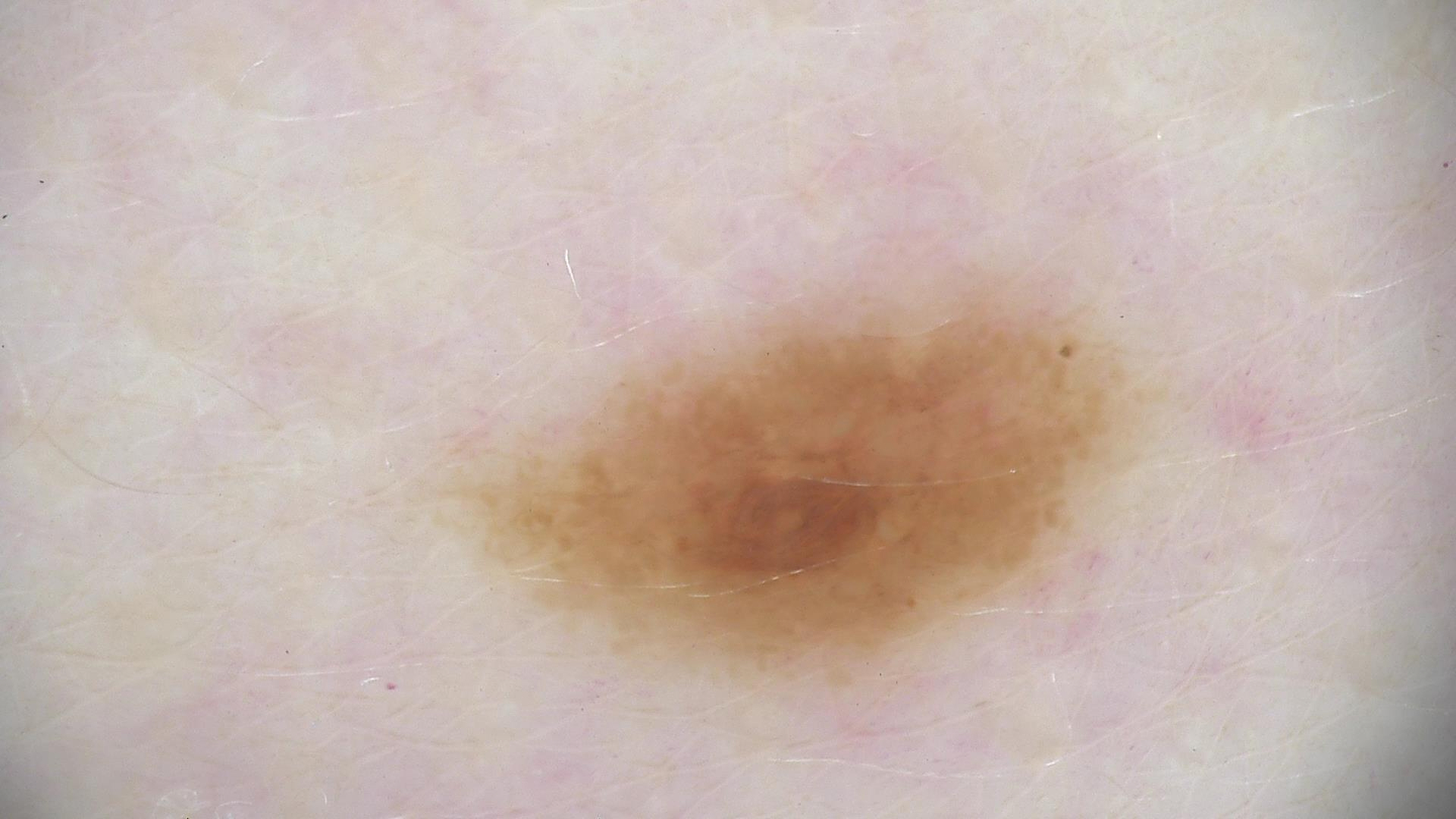{
  "image": "dermatoscopy",
  "diagnosis": {
    "name": "compound nevus",
    "code": "cb",
    "malignancy": "benign",
    "super_class": "melanocytic",
    "confirmation": "expert consensus"
  }
}